A dermatoscopic image of a skin lesion — 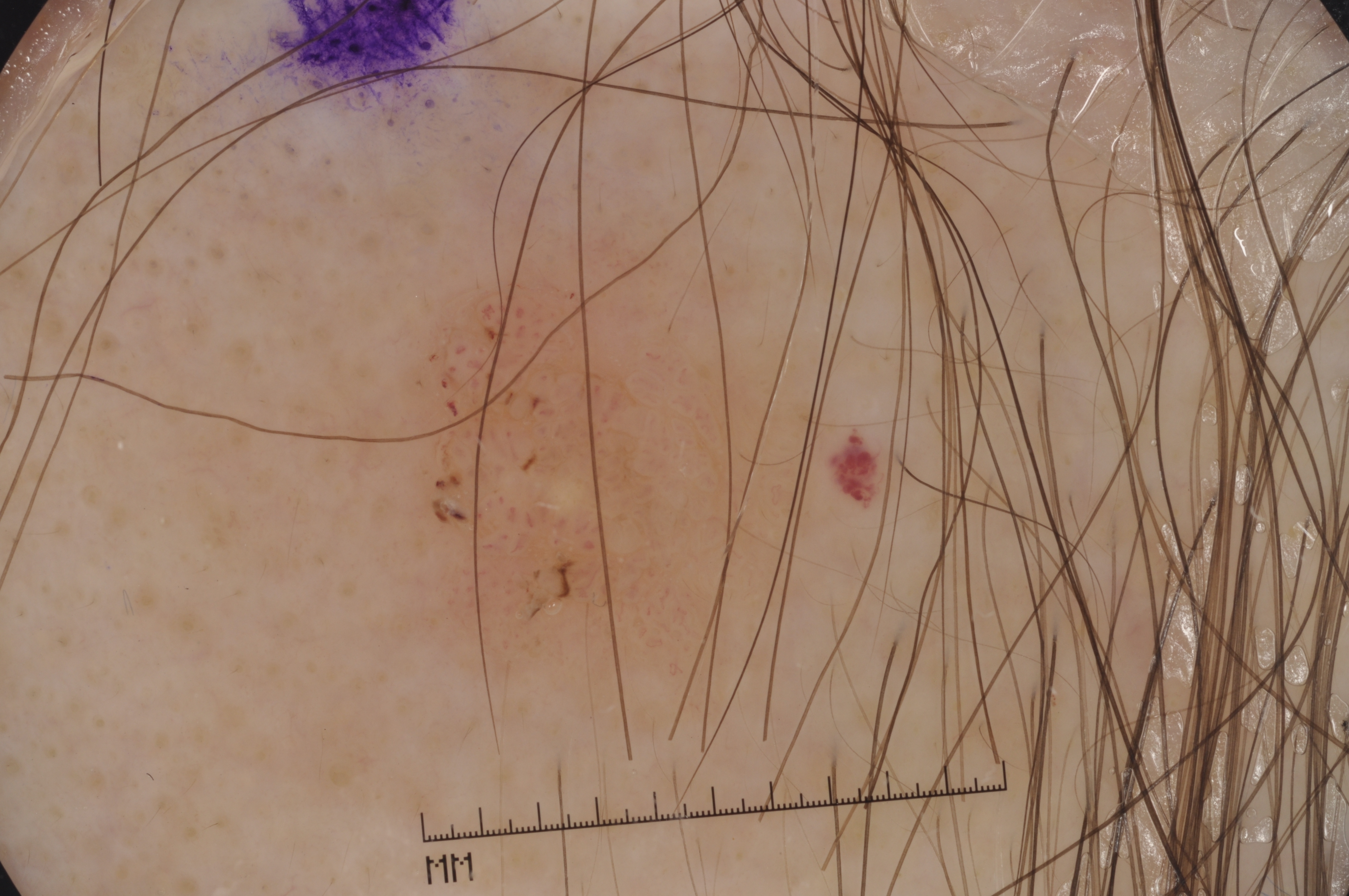lesion_location:
  bbox_xyxy:
    - 393
    - 272
    - 818
    - 730
dermoscopic_features:
  present: []
  absent:
    - pigment network
    - streaks
    - negative network
    - milia-like cysts
diagnosis:
  name: seborrheic keratosis
  malignancy: benign
  lineage: keratinocytic
  provenance: clinical